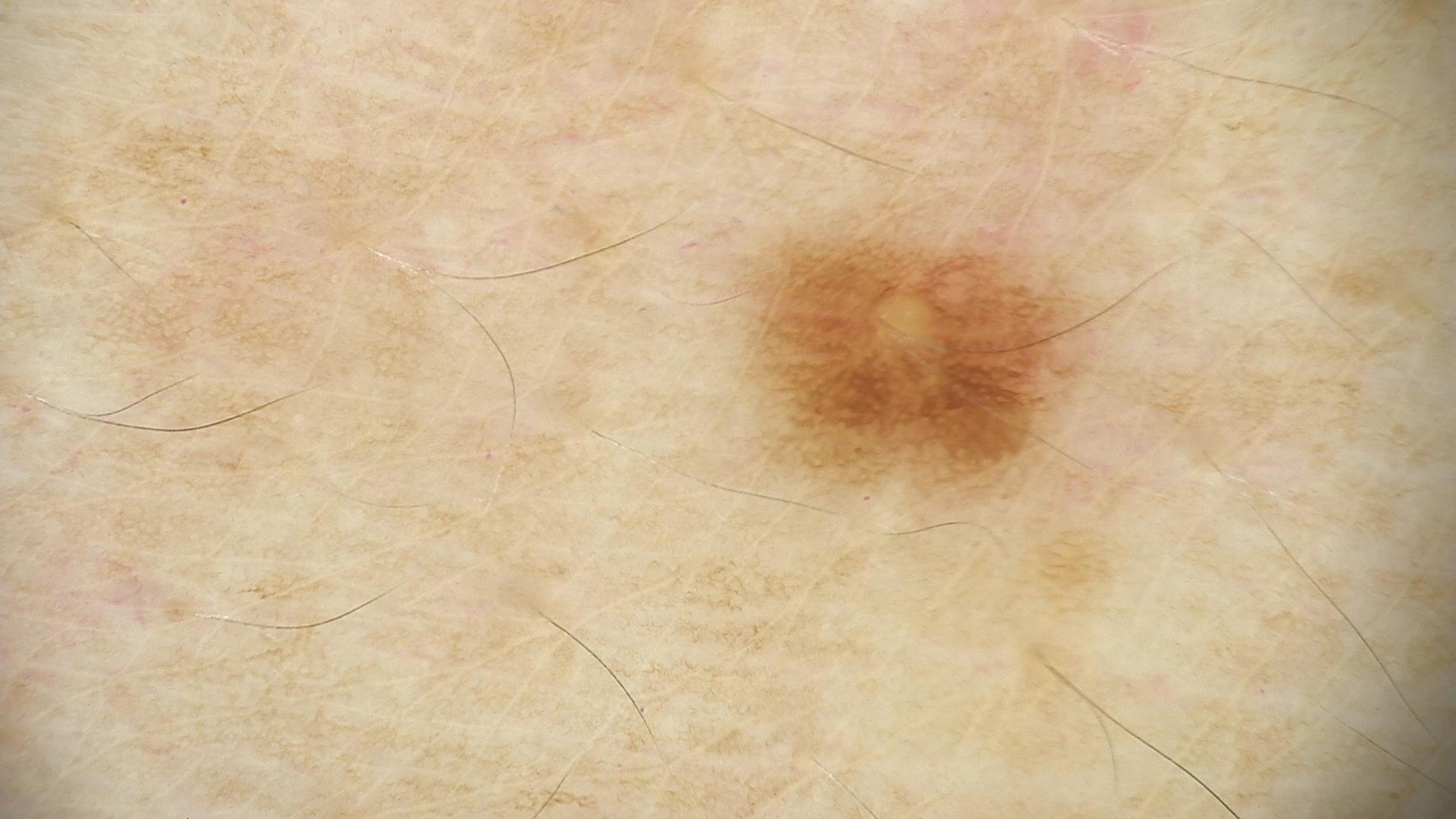A dermatoscopic image of a skin lesion.
The morphology is that of a banal lesion.
Consistent with a junctional nevus.